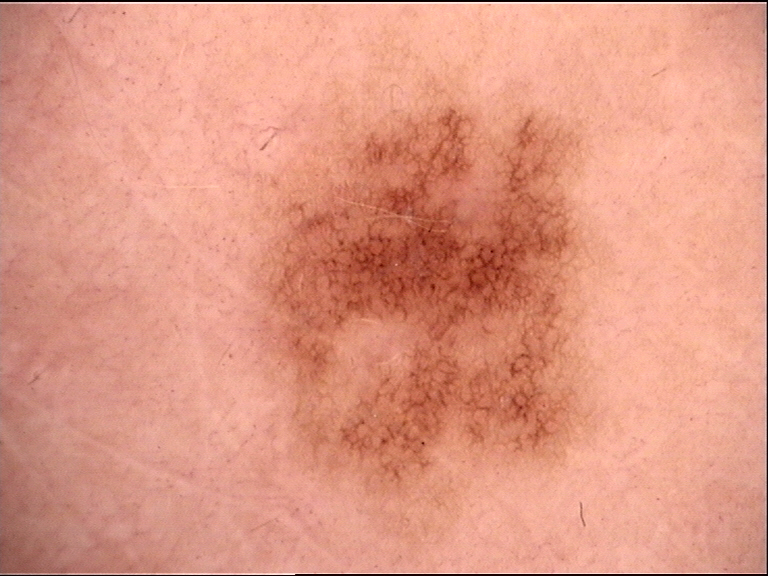- imaging — dermatoscopy
- class — dysplastic junctional nevus (expert consensus)